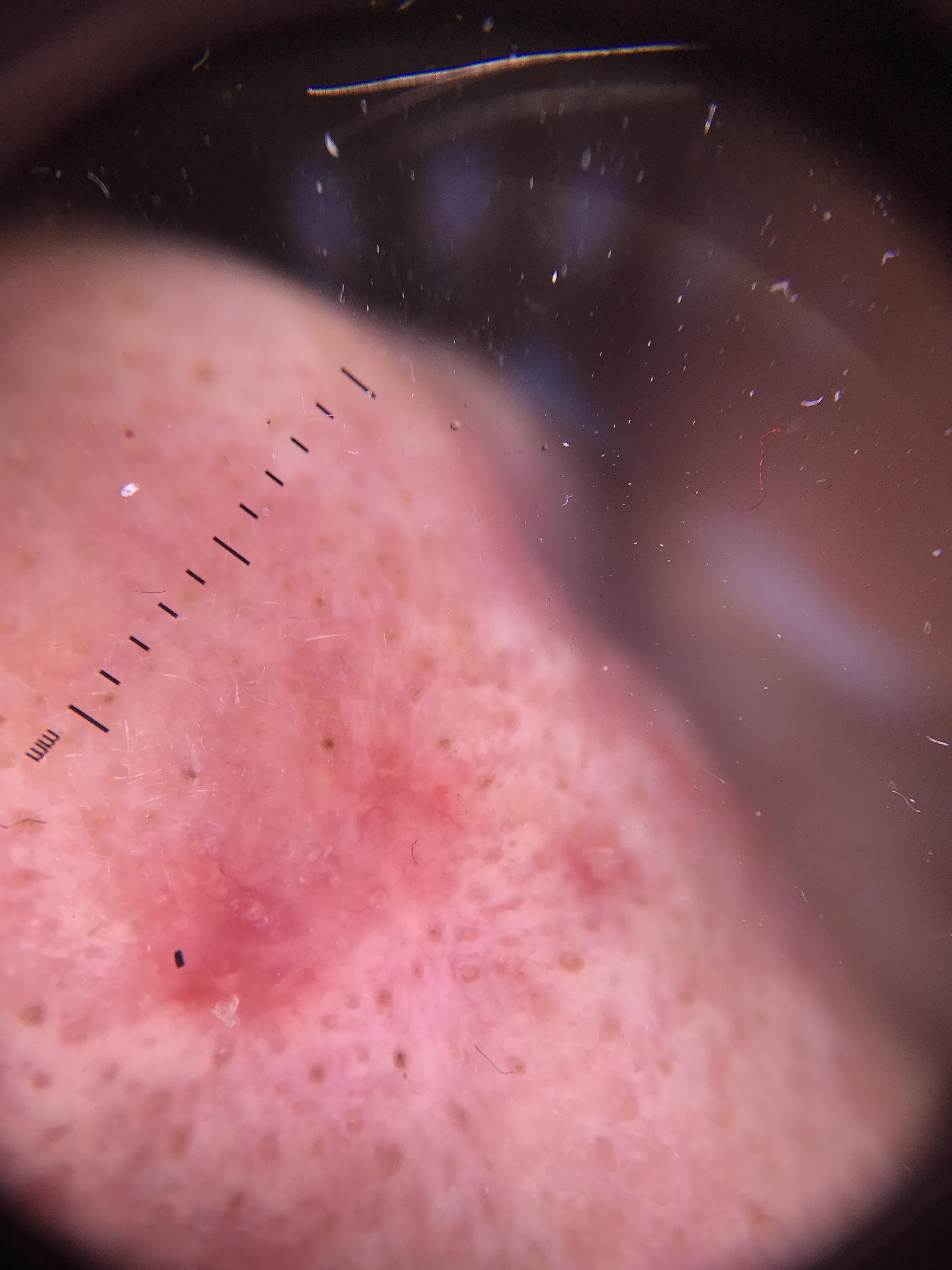A dermoscopic photograph of a skin lesion. The chart notes a prior melanoma but no first-degree relative with melanoma. A female subject in their mid- to late 70s. Located on the head or neck. Histopathology confirmed a malignant lesion — a basal cell carcinoma.